The subject is a female aged 50–59 · an image taken at an angle · located on the front of the torso and head or neck · reported lesion symptoms include itching · the patient reports the lesion is raised or bumpy · Fitzpatrick skin type III · reported duration is about one day · the patient described the issue as a rash:
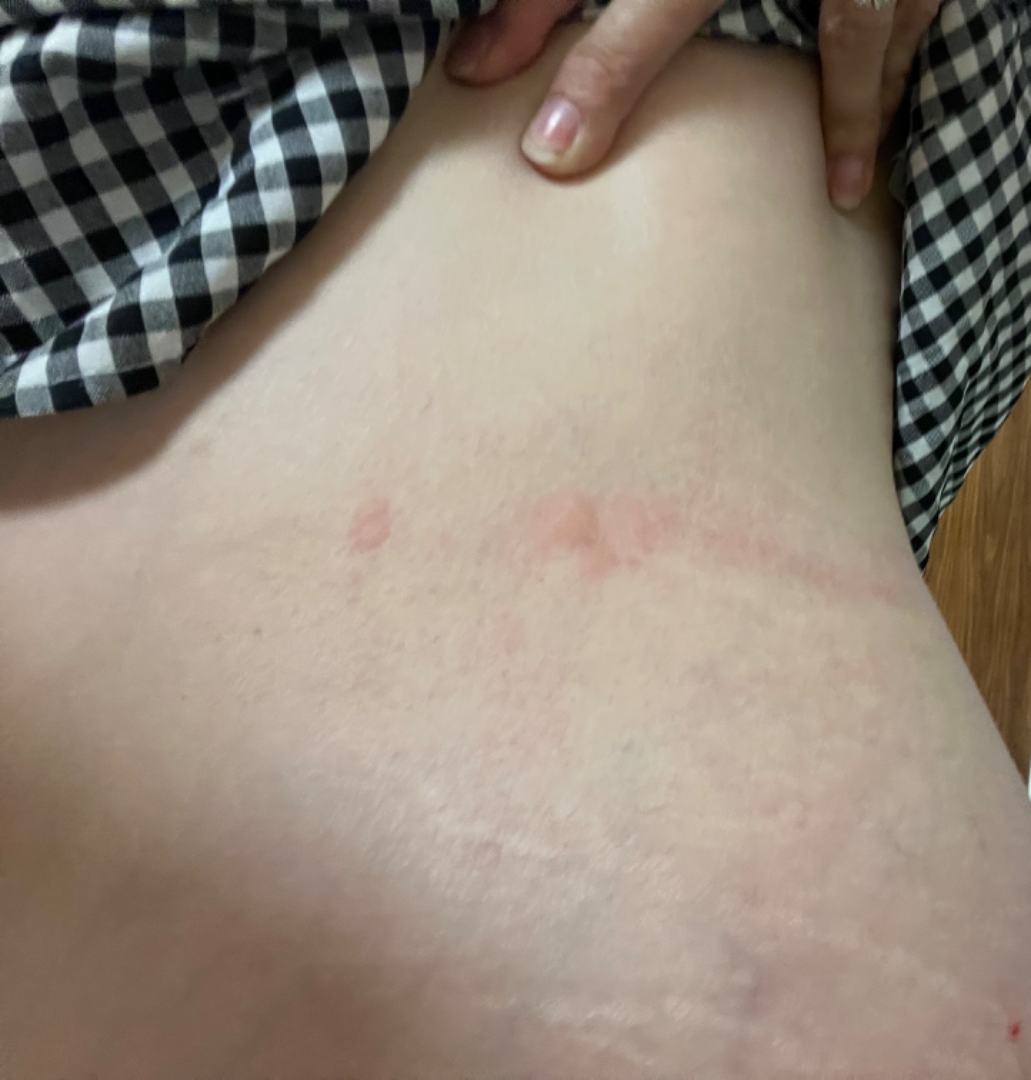Impression:
The reviewing clinician's impression was: in keeping with Urticaria.